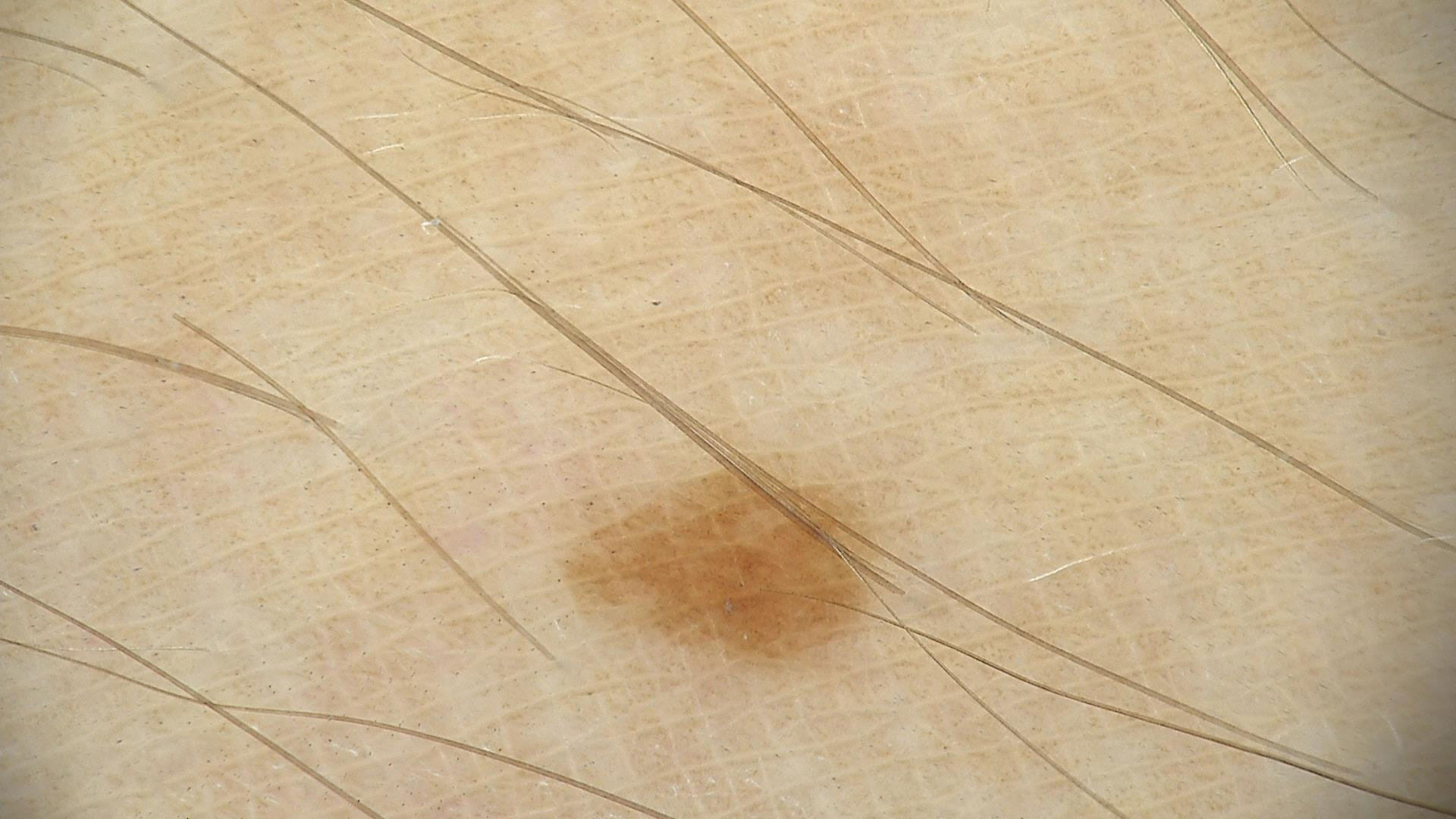{"image": "dermatoscopy", "diagnosis": {"name": "dysplastic junctional nevus", "code": "jd", "malignancy": "benign", "super_class": "melanocytic", "confirmation": "expert consensus"}}